A patient in their 60s; a clinical photo of a skin lesion taken with a smartphone: 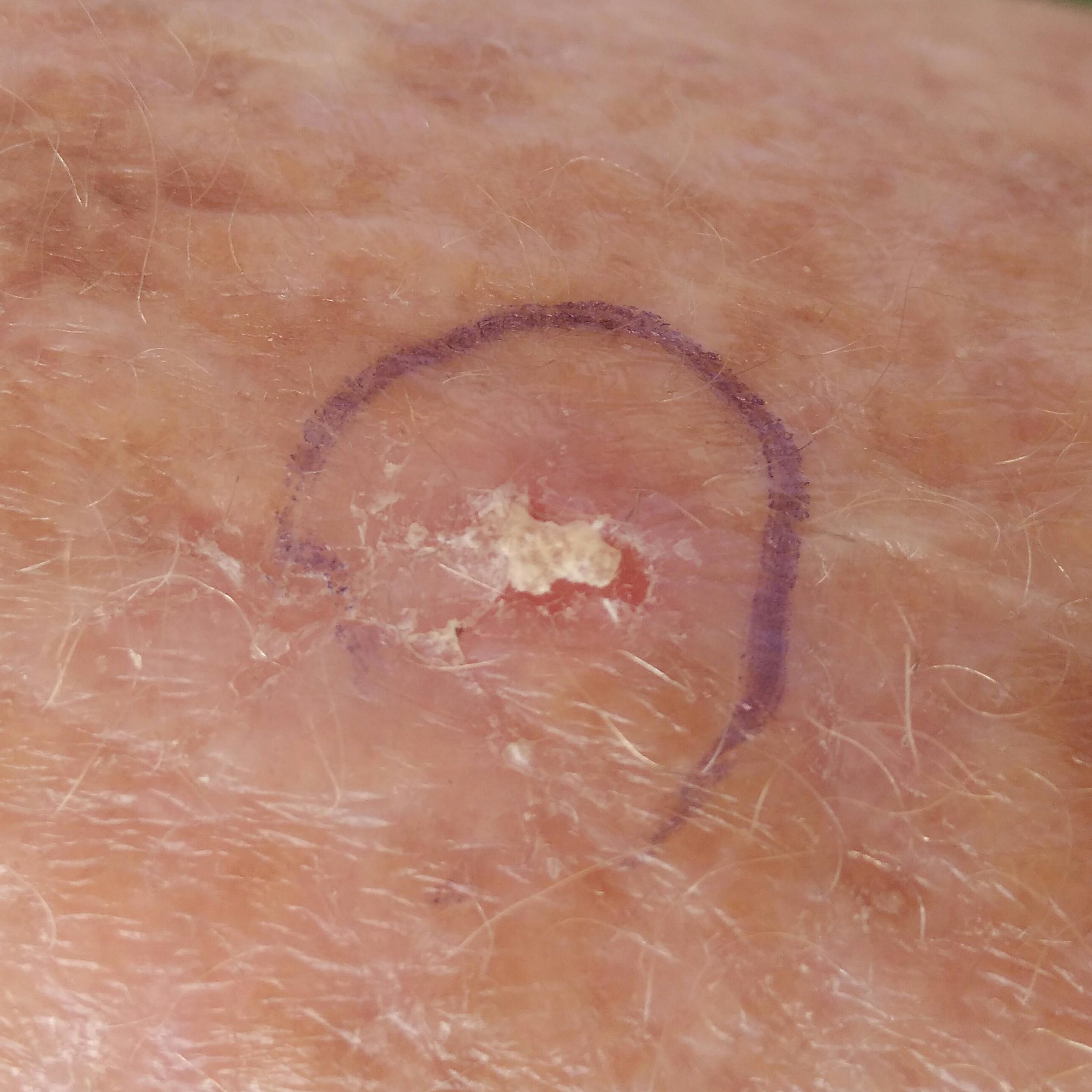The lesion is located on a forearm. Per patient report, the lesion itches and is elevated, but has not grown. Consistent with a premalignant lesion — an actinic keratosis.